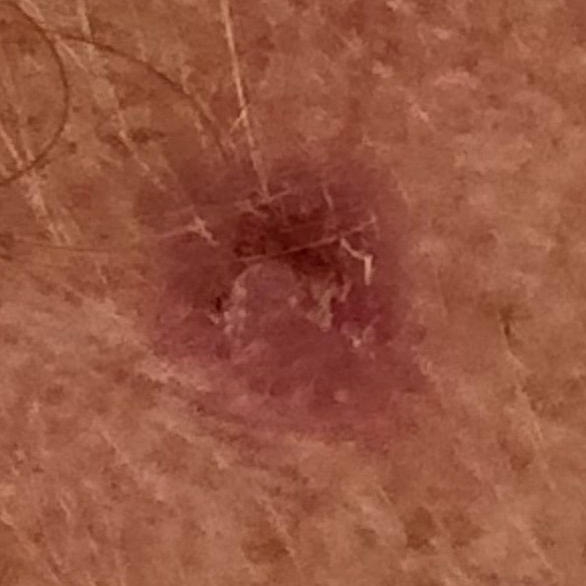Patient and lesion: Located on the chest. Conclusion: The biopsy diagnosis was a basal cell carcinoma.